This is a close-up image.
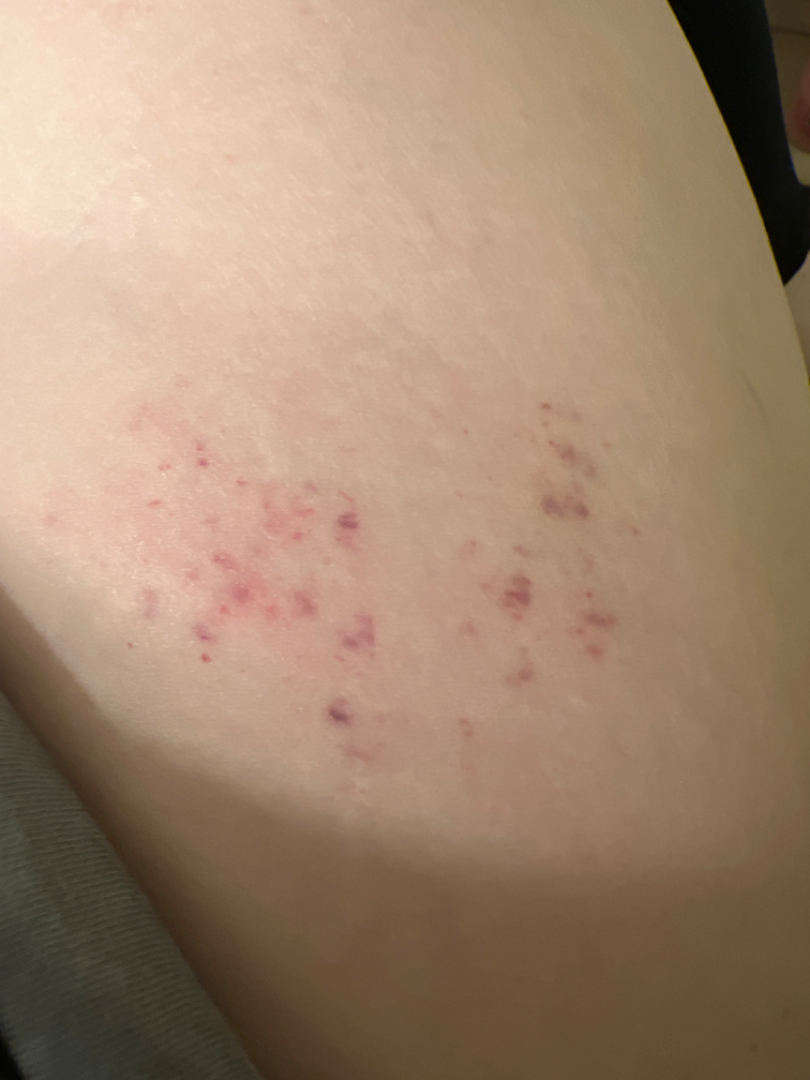Case summary:
• assessment · indeterminate from the photograph